The patient is a female aged 60–69, self-categorized by the patient as a rash, located on the arm, a close-up photograph: 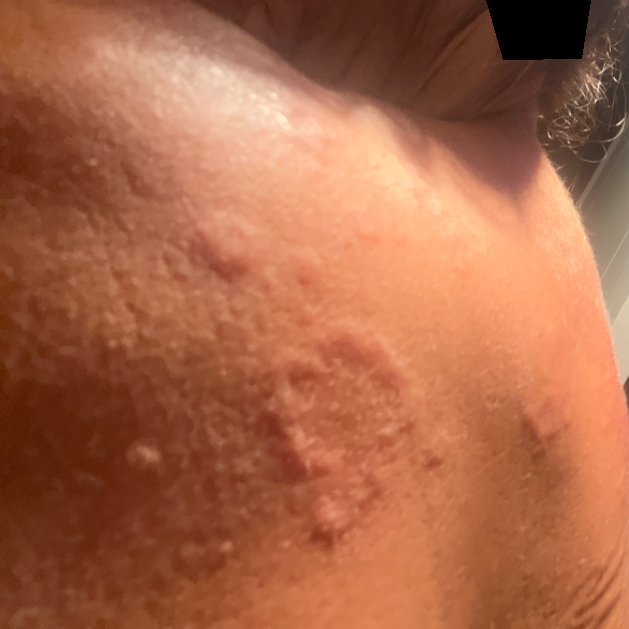Findings:
Single-reviewer assessment: consistent with Urticaria.